Dermoscopy of a skin lesion.
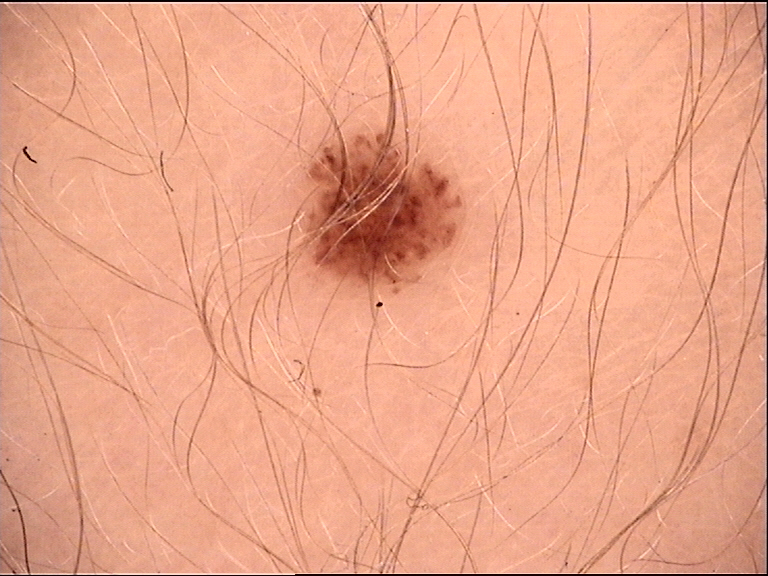diagnostic label=dysplastic junctional nevus (expert consensus).